A clinical photo of a skin lesion taken with a smartphone · FST I · the chart notes pesticide exposure, prior malignancy (patient or family), tobacco use, no prior skin cancer (patient or family), and no alcohol use: 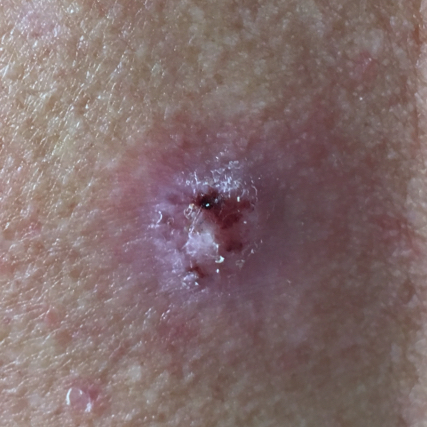The lesion involves the back.
The lesion measures 12 × 9 mm.
Per patient report, the lesion has bled, itches, is elevated, and hurts, but has not grown and has not changed.
Biopsy-confirmed as a basal cell carcinoma.